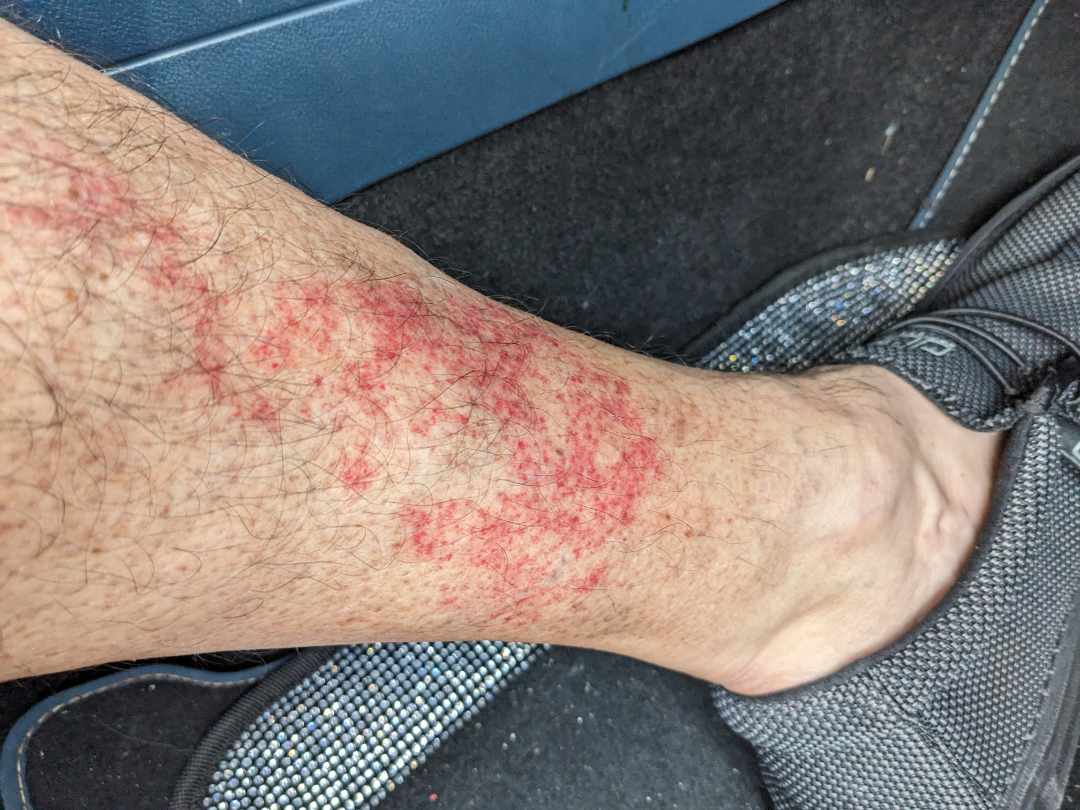The reviewing dermatologist was unable to assign a differential diagnosis from the image.